A dermoscopy image of a single skin lesion: 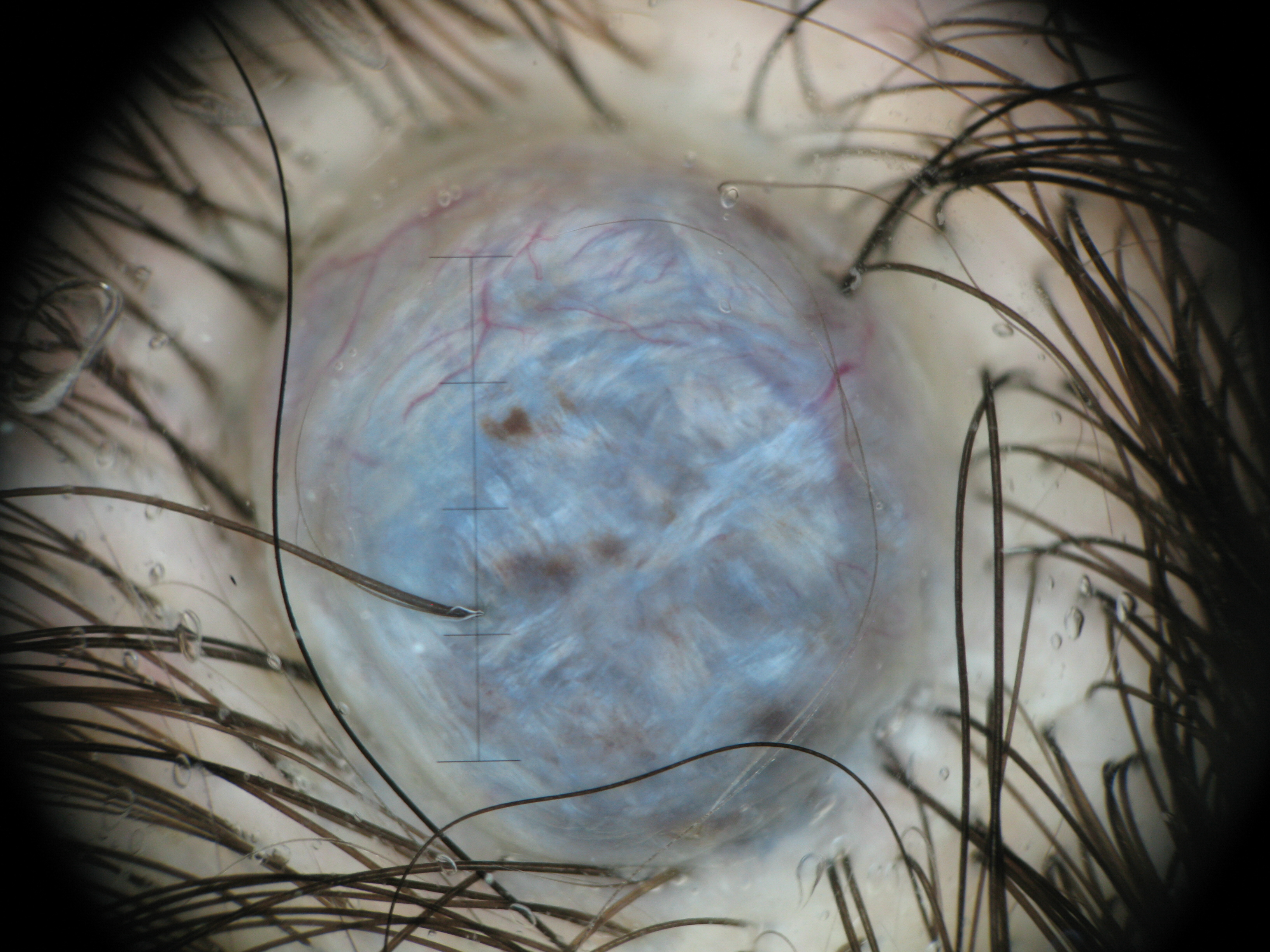label = blue nevus (expert consensus).